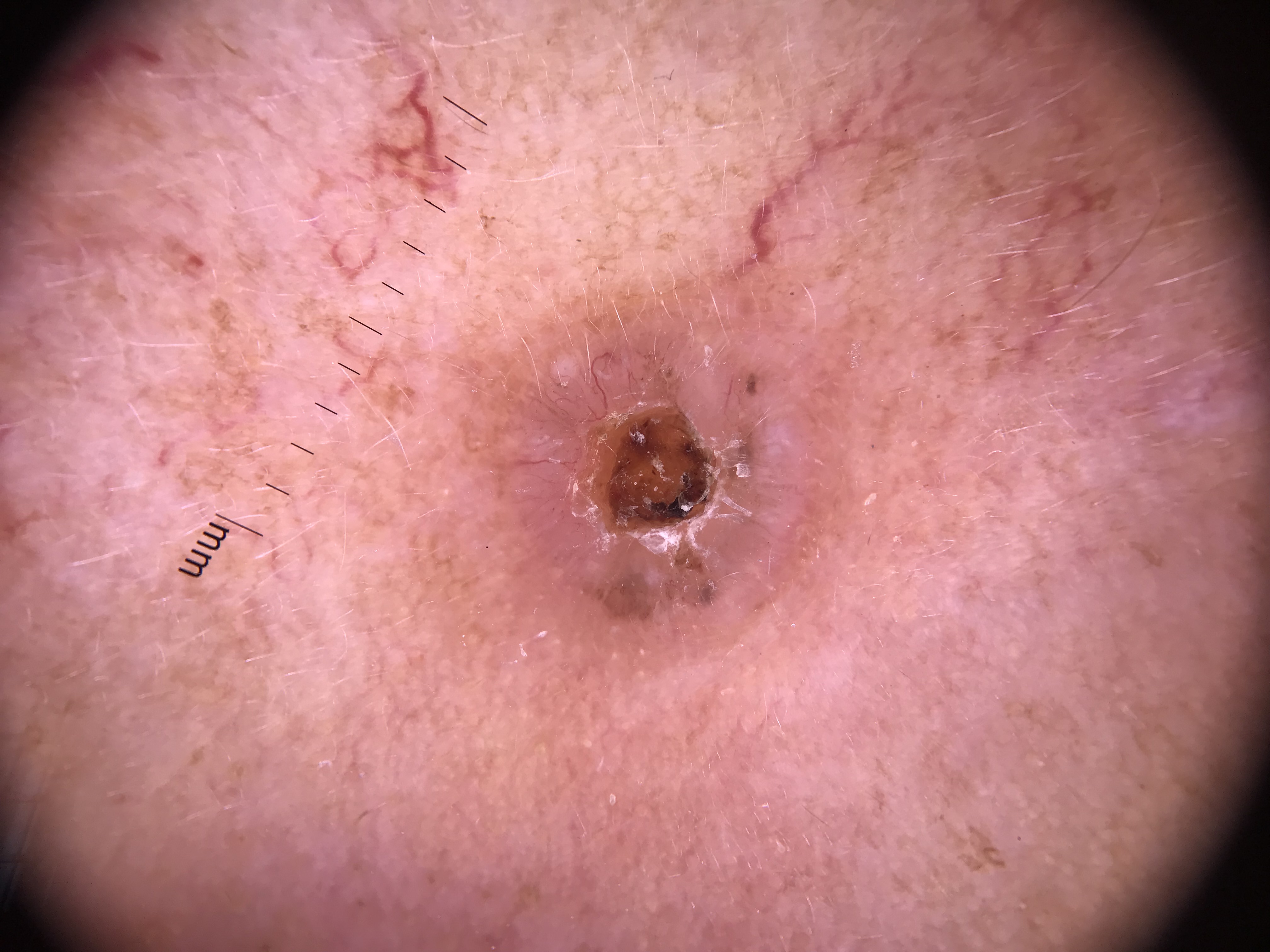Findings:
– diagnostic label: basal cell carcinoma (biopsy-proven)